A dermoscopic photograph of a skin lesion:
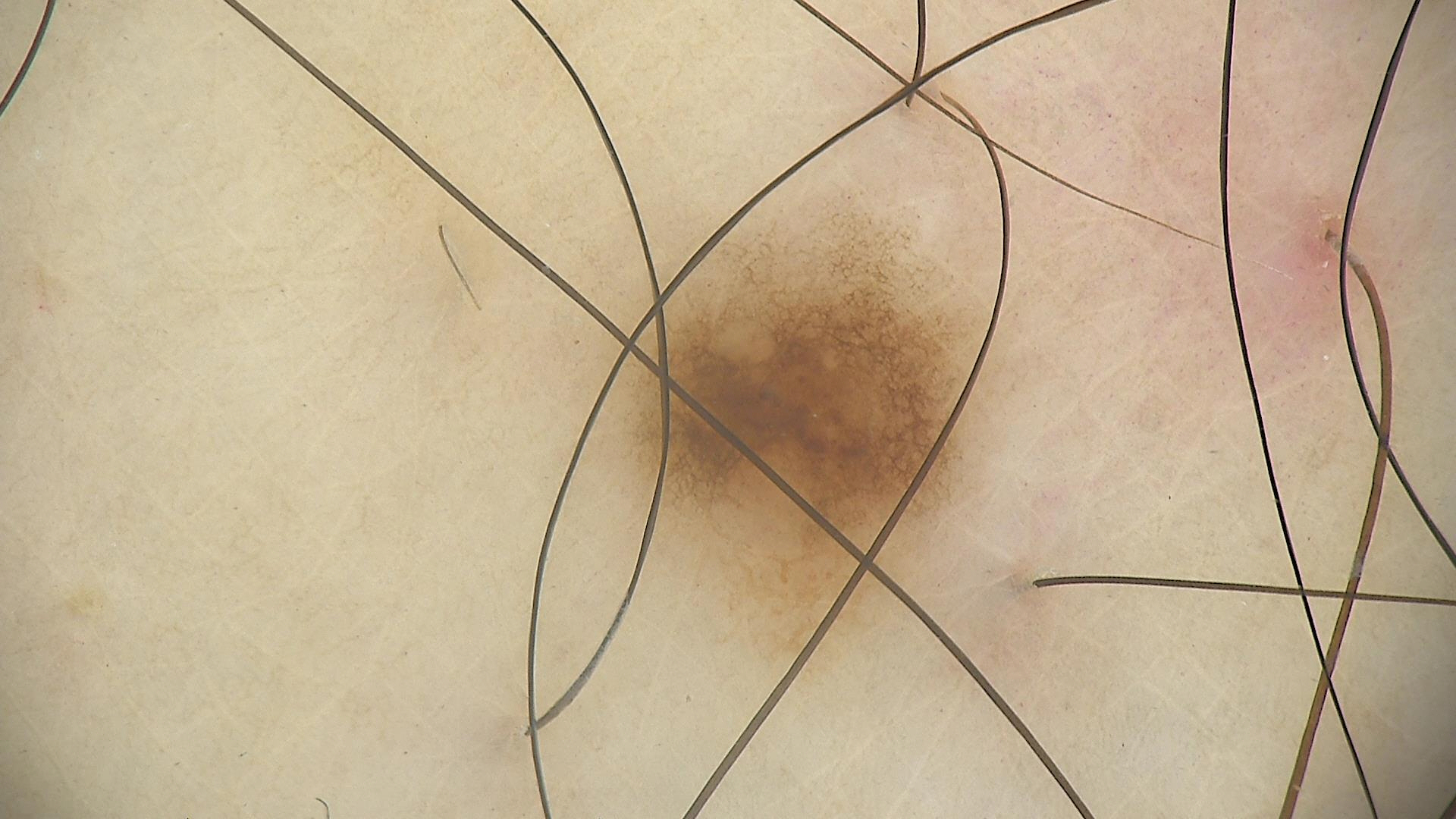Impression: Labeled as a dysplastic junctional nevus.